A close-up photograph.
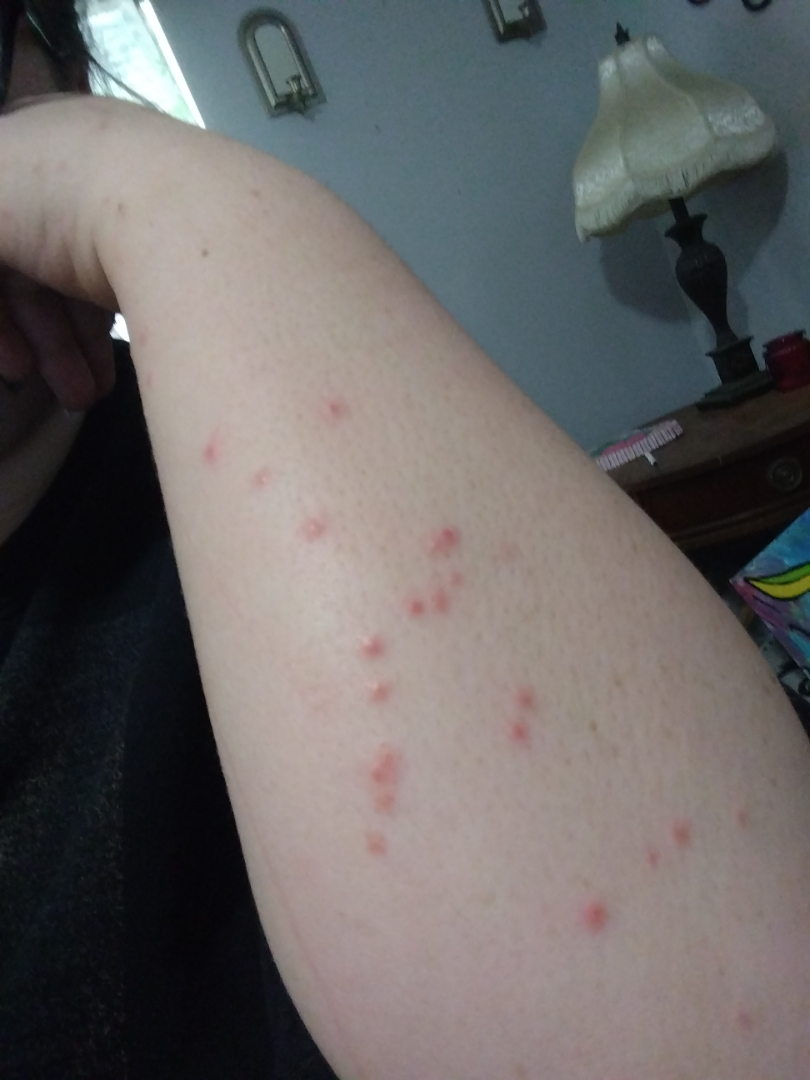impression: most consistent with Insect Bite; an alternative is Eczema; with consideration of Molluscum Contagiosum.